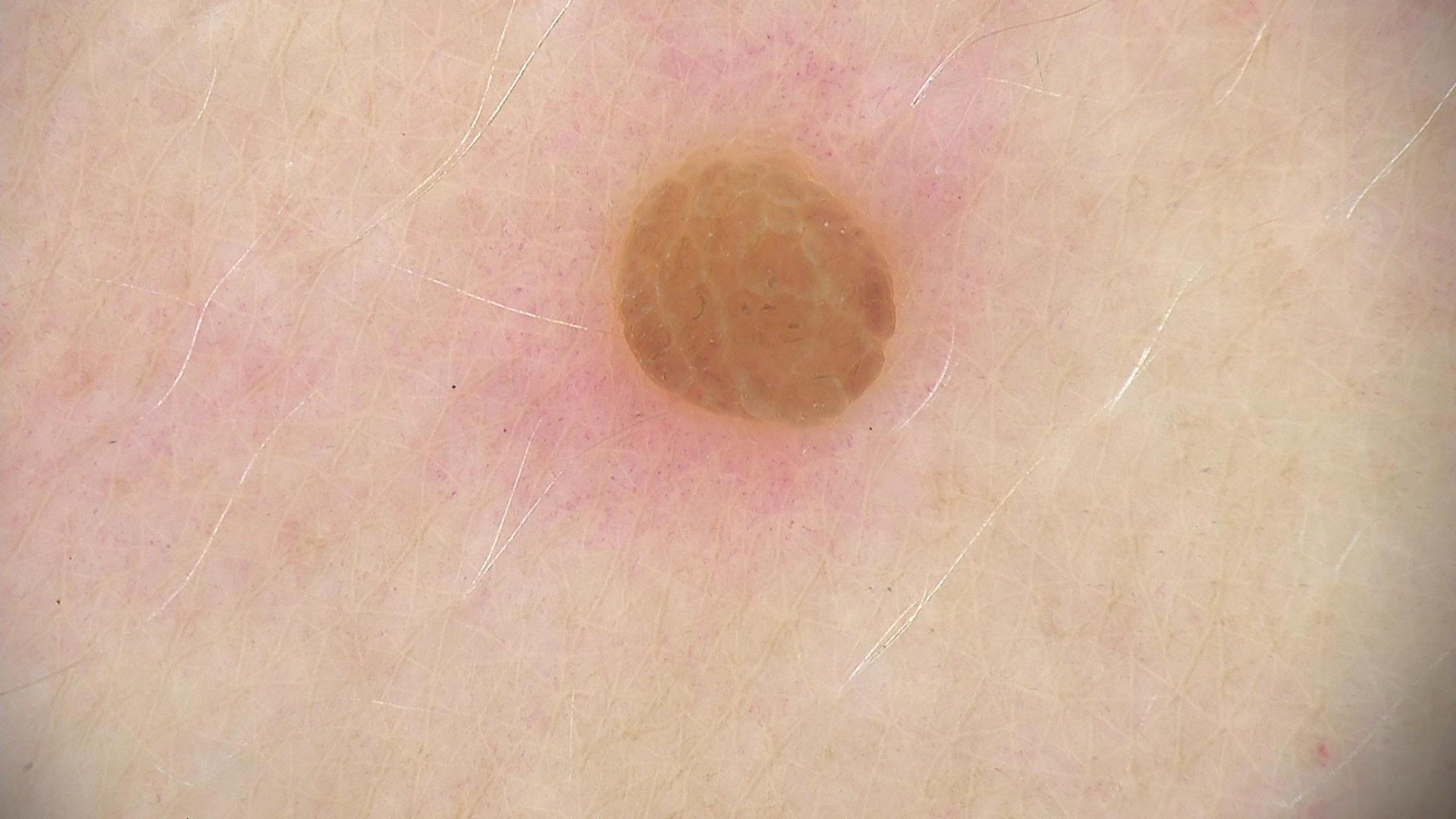assessment — dermal nevus (expert consensus).